The chart records a first-degree relative with melanoma · Fitzpatrick III · a male patient in their 40s · a contact-polarized dermoscopy image of a skin lesion — 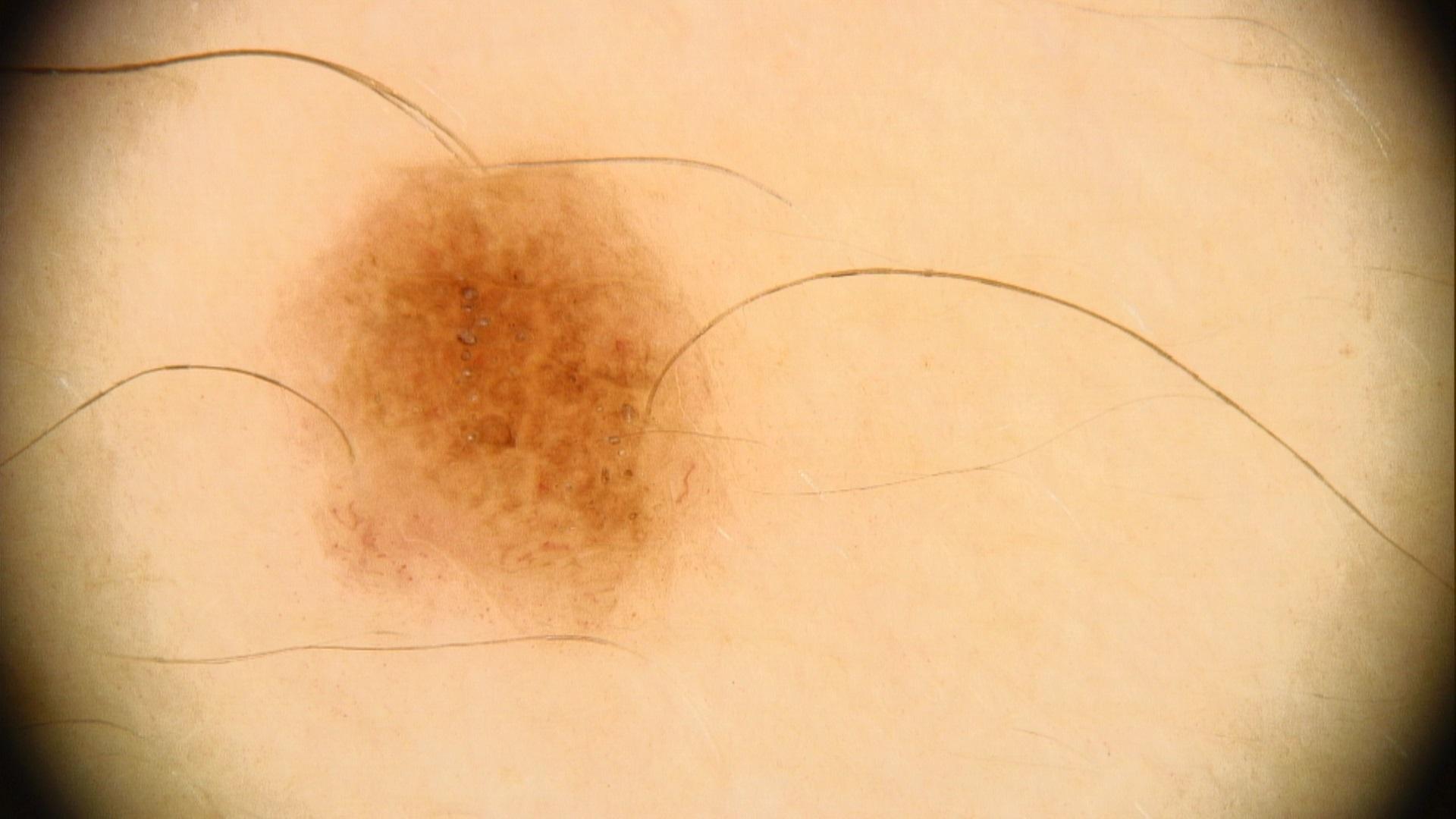{"lesion_location": {"region": "the trunk", "detail": "the anterior trunk"}, "diagnosis": {"name": "Nevus", "malignancy": "benign", "confirmation": "expert clinical impression", "lineage": "melanocytic"}}